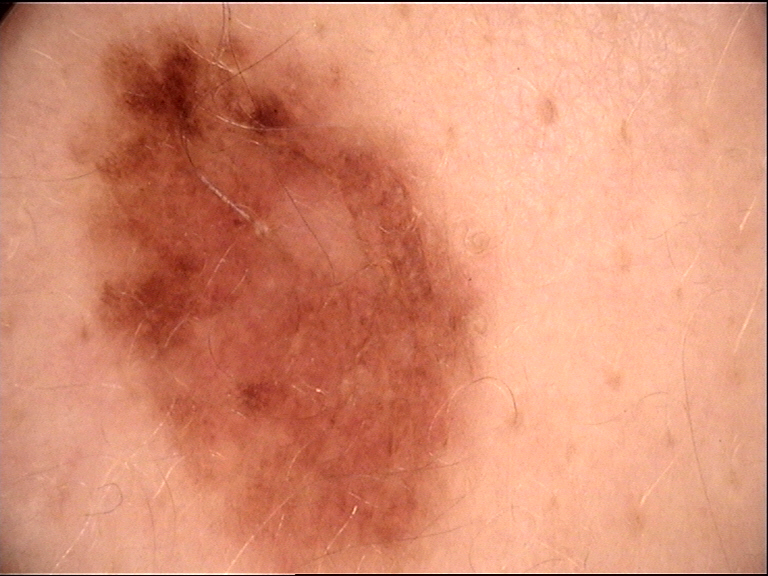A dermoscopic image of a skin lesion.
Consistent with a dysplastic compound nevus.